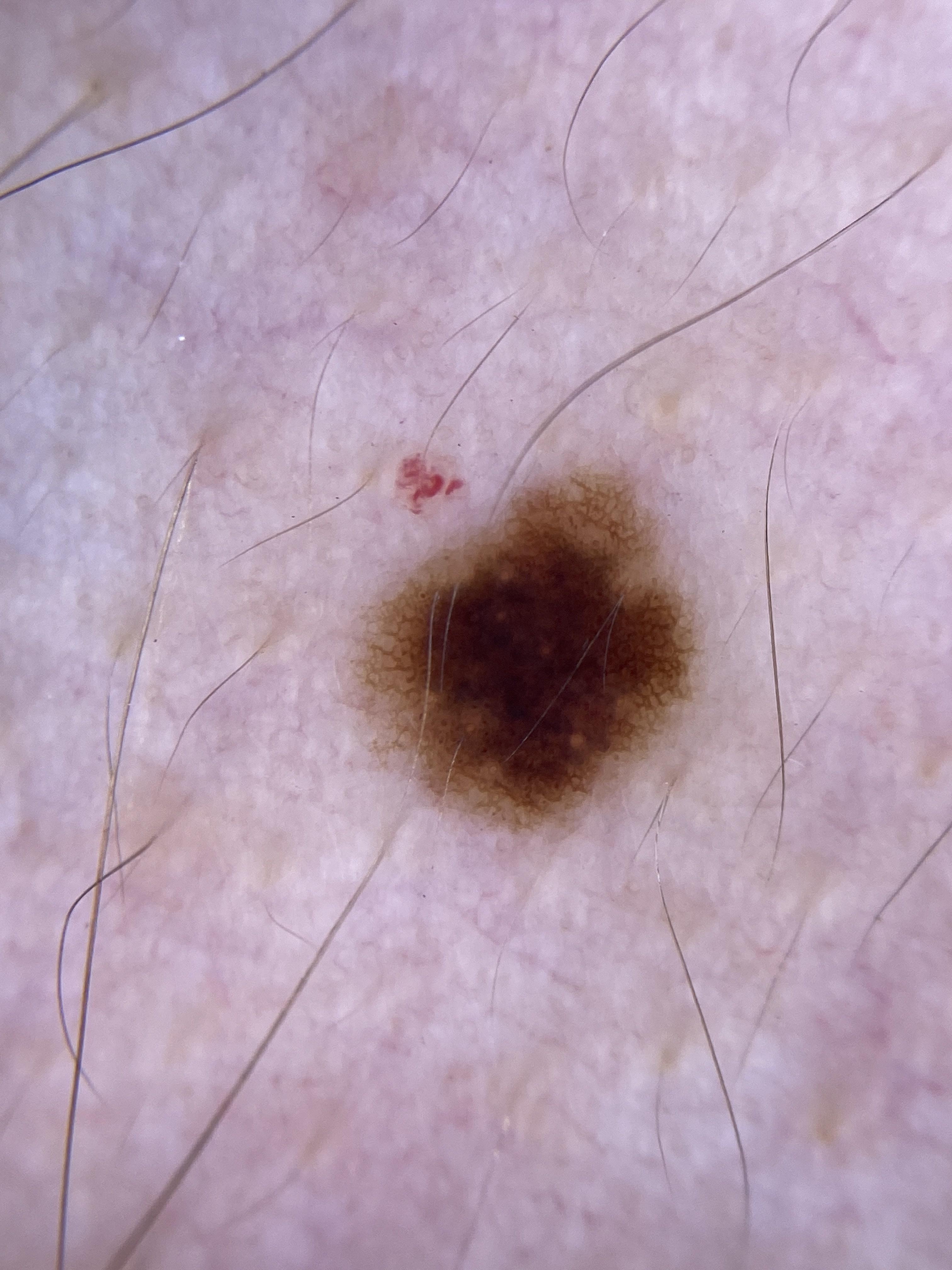{
  "patient": {
    "age_approx": 20,
    "sex": "male"
  },
  "skin_type": "II",
  "melanoma_history": {
    "family_hx_melanoma": true
  },
  "lesion_location": {
    "region": "the trunk",
    "detail": "the anterior trunk"
  },
  "diagnosis": {
    "name": "Nevus",
    "malignancy": "benign",
    "confirmation": "expert clinical impression",
    "lineage": "melanocytic"
  }
}